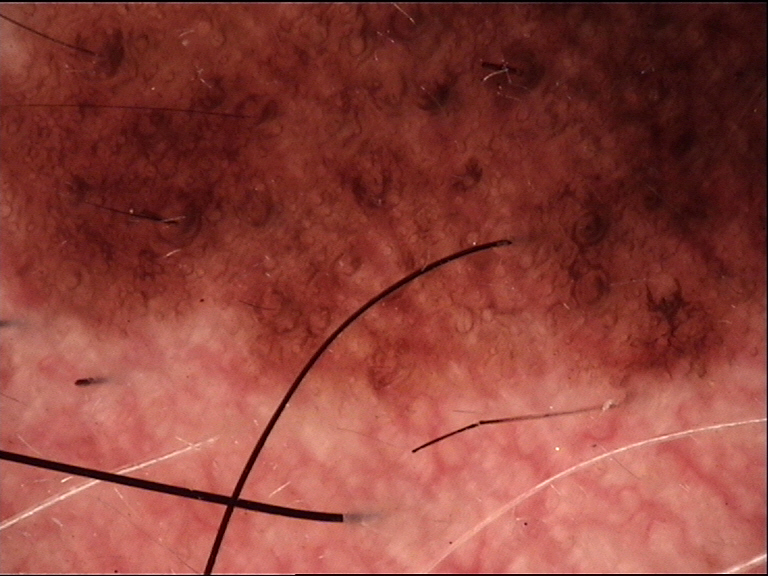Confirmed on histopathology as a lentigo maligna.